The photo was captured at an angle.
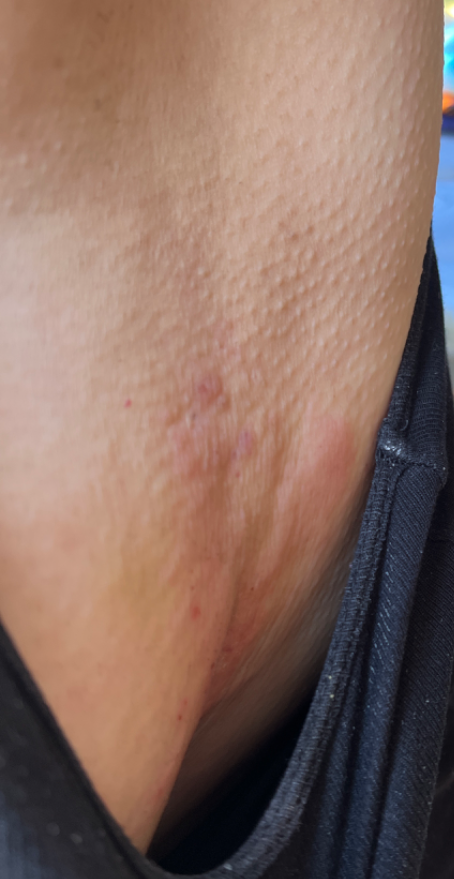The skin findings could not be characterized from the image.
Texture is reported as raised or bumpy.
The patient described the issue as a rash.
Reported lesion symptoms include bothersome appearance, darkening, enlargement and itching.
Reported duration is less than one week.
Lay reviewers estimated Monk skin tone scale 2 or 5.